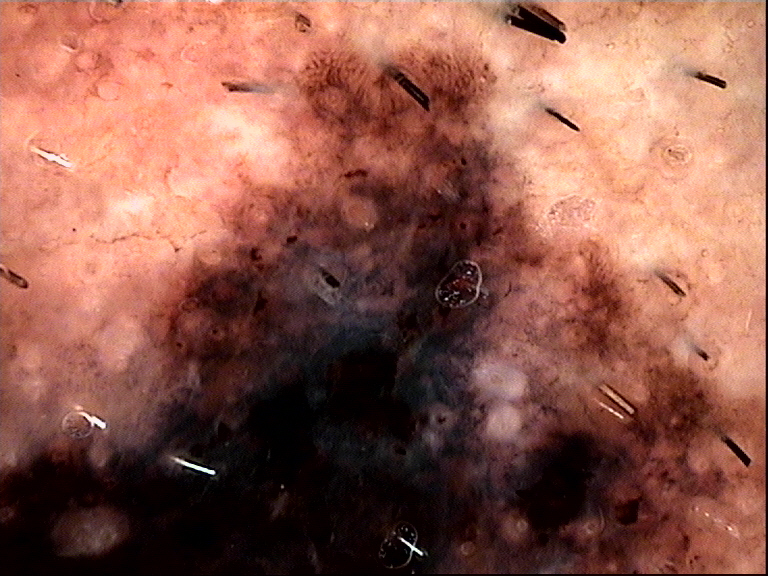diagnostic label = lentigo maligna melanoma (biopsy-proven).